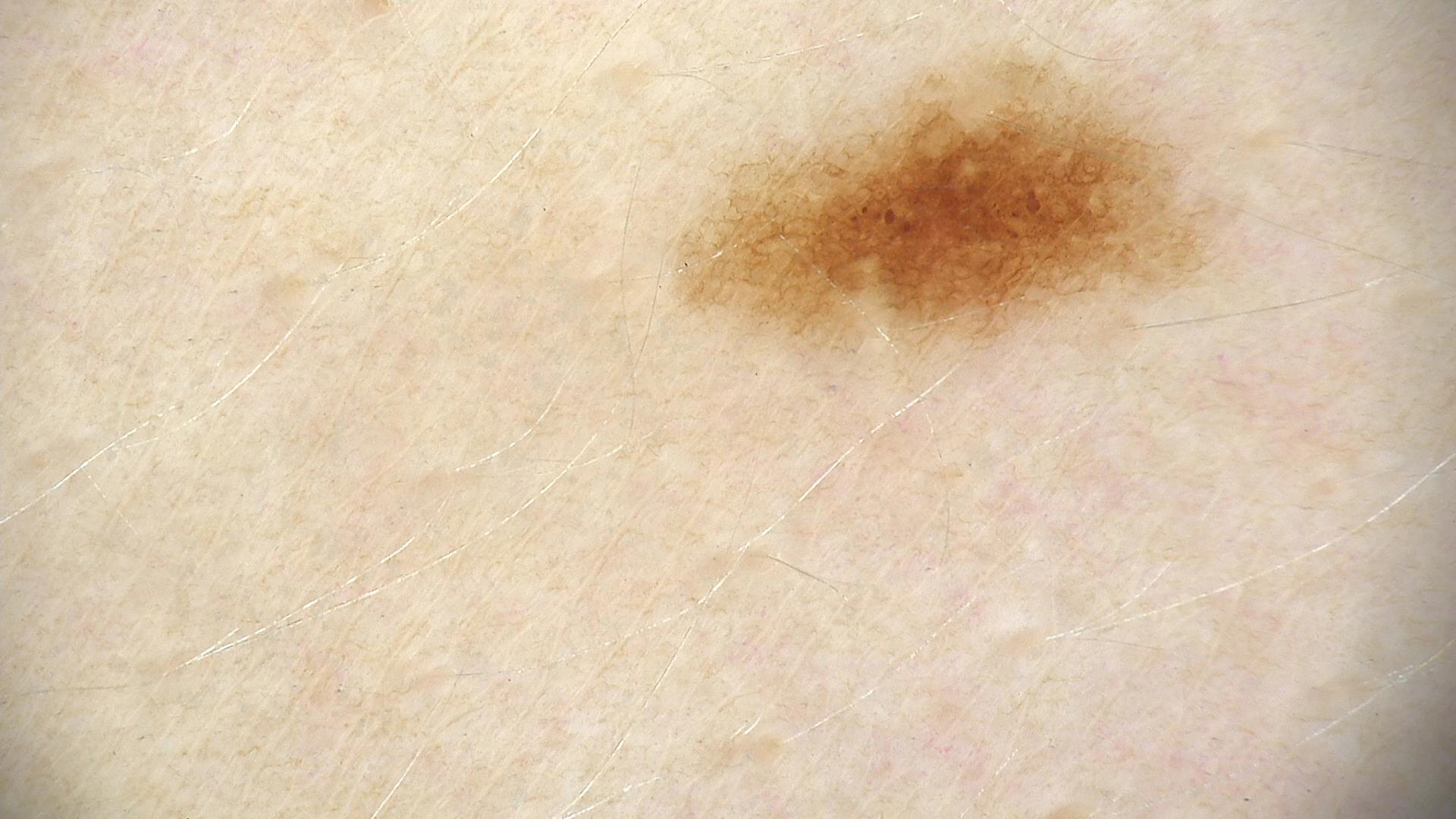The diagnostic label was a dysplastic junctional nevus.